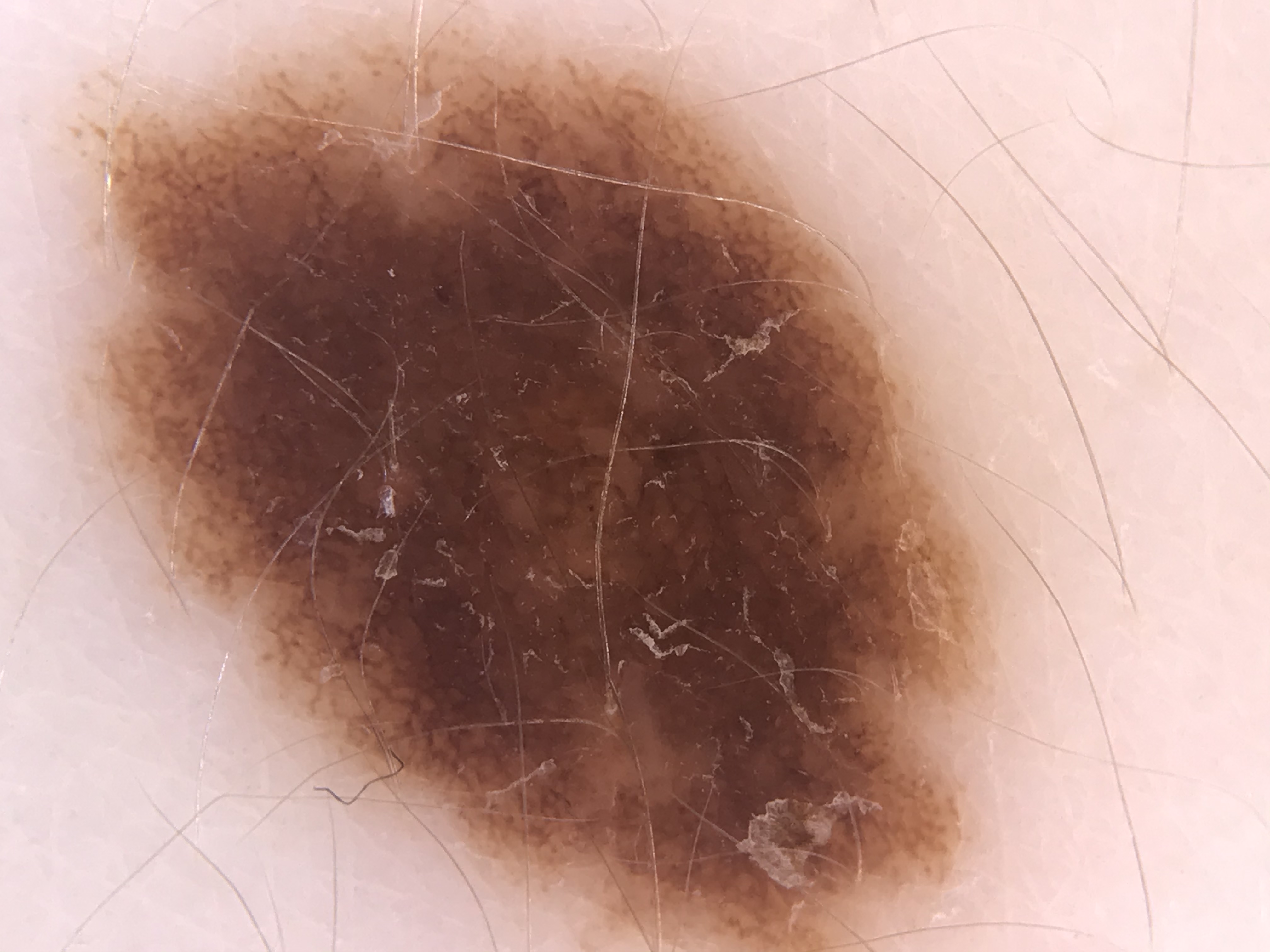Diagnosed as a dysplastic compound nevus.